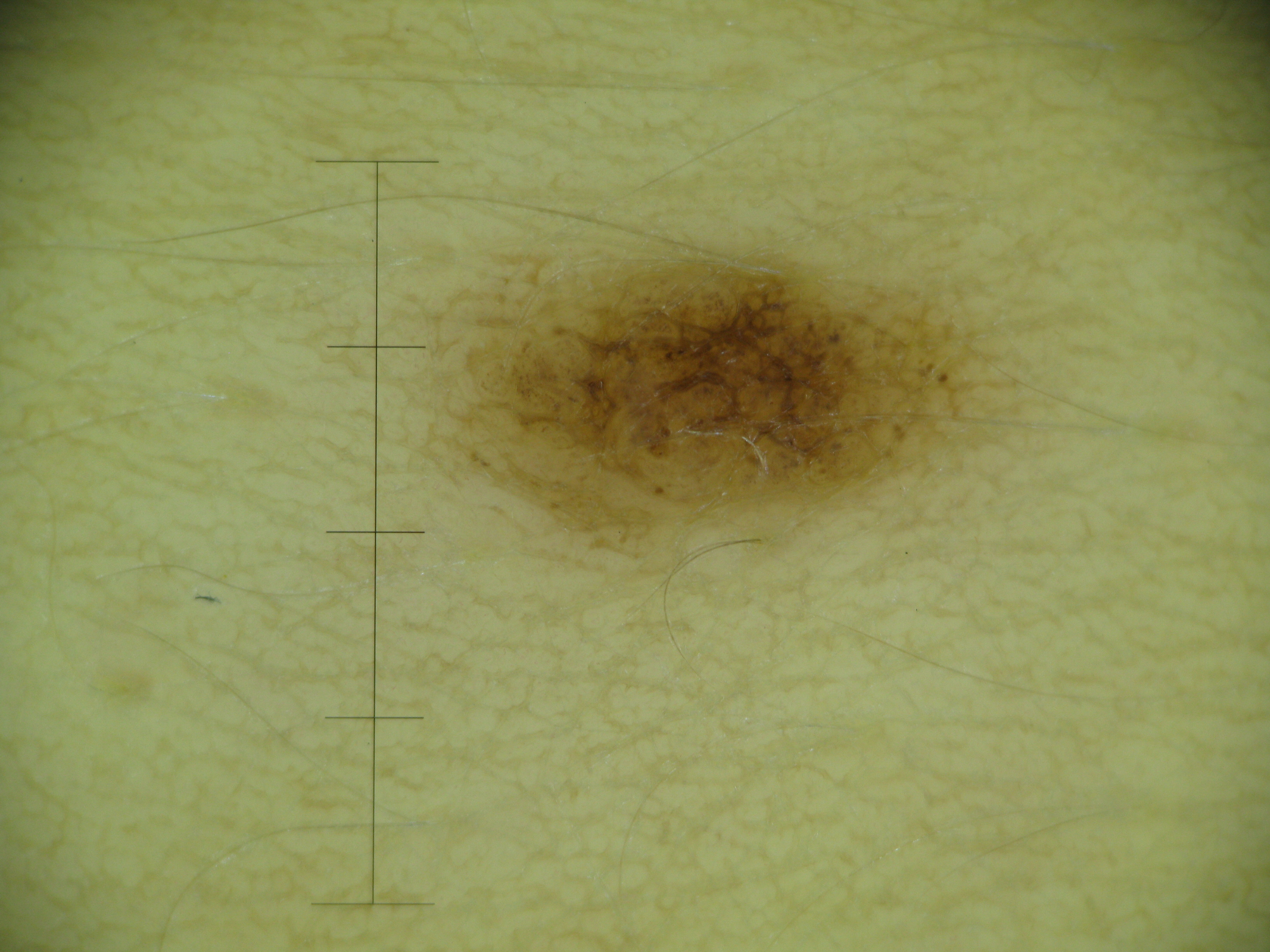Classified as a dysplastic junctional nevus.